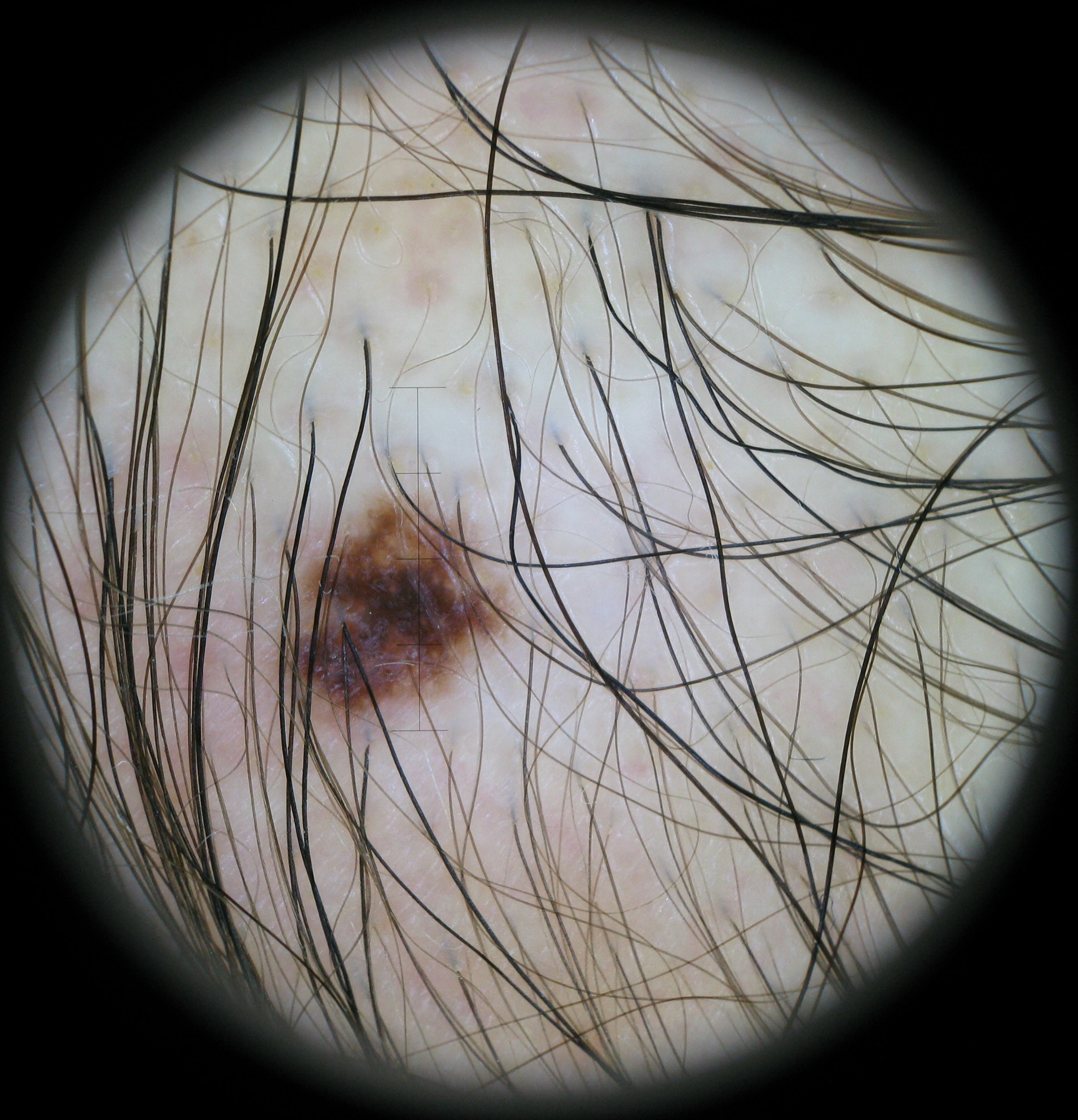<case>
  <diagnosis>
    <name>dysplastic junctional nevus</name>
    <code>jd</code>
    <malignancy>benign</malignancy>
    <super_class>melanocytic</super_class>
    <confirmation>expert consensus</confirmation>
  </diagnosis>
</case>